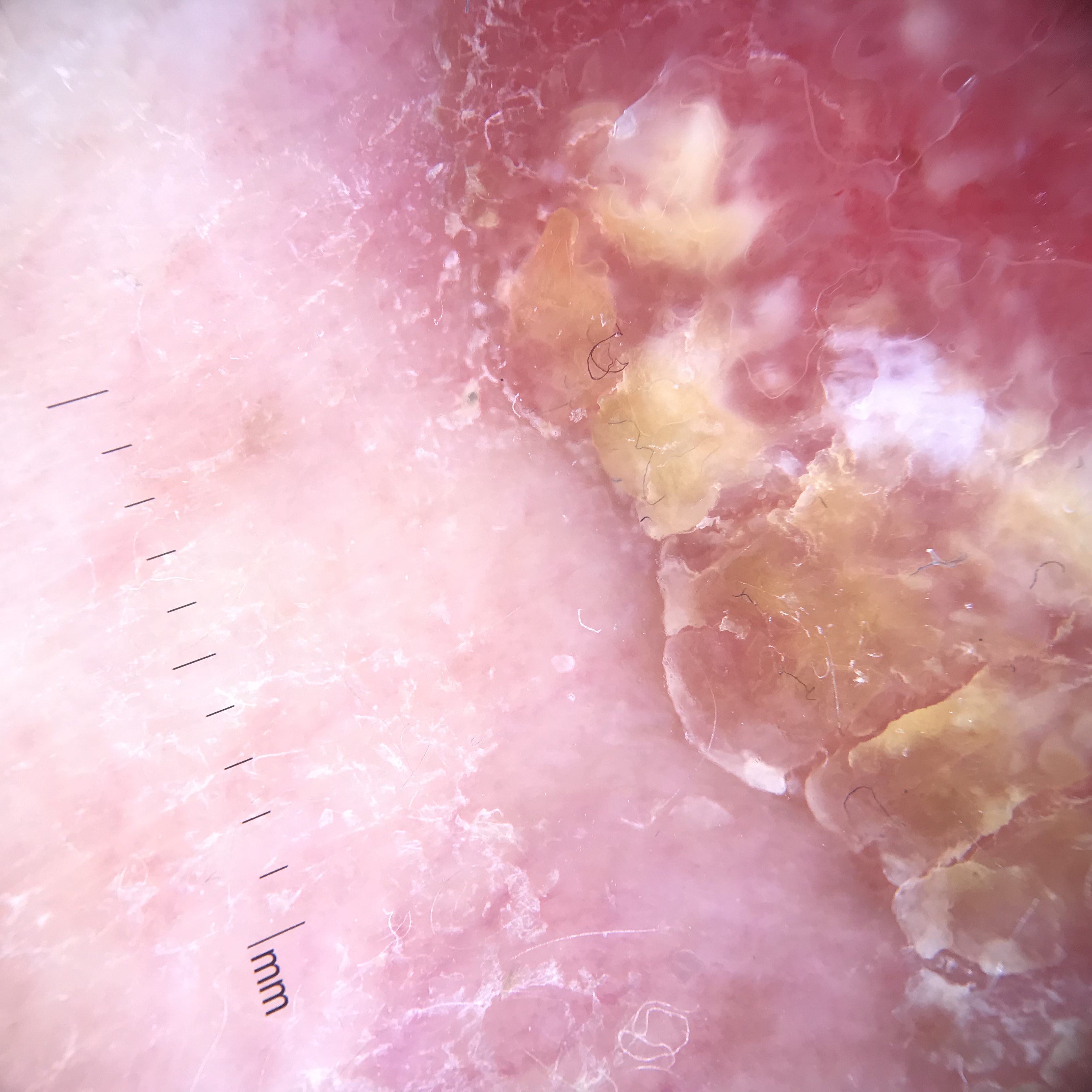A dermoscopic close-up of a skin lesion.
This is a keratinocytic lesion.
Histopathologically confirmed as a skin cancer — a squamous cell carcinoma.